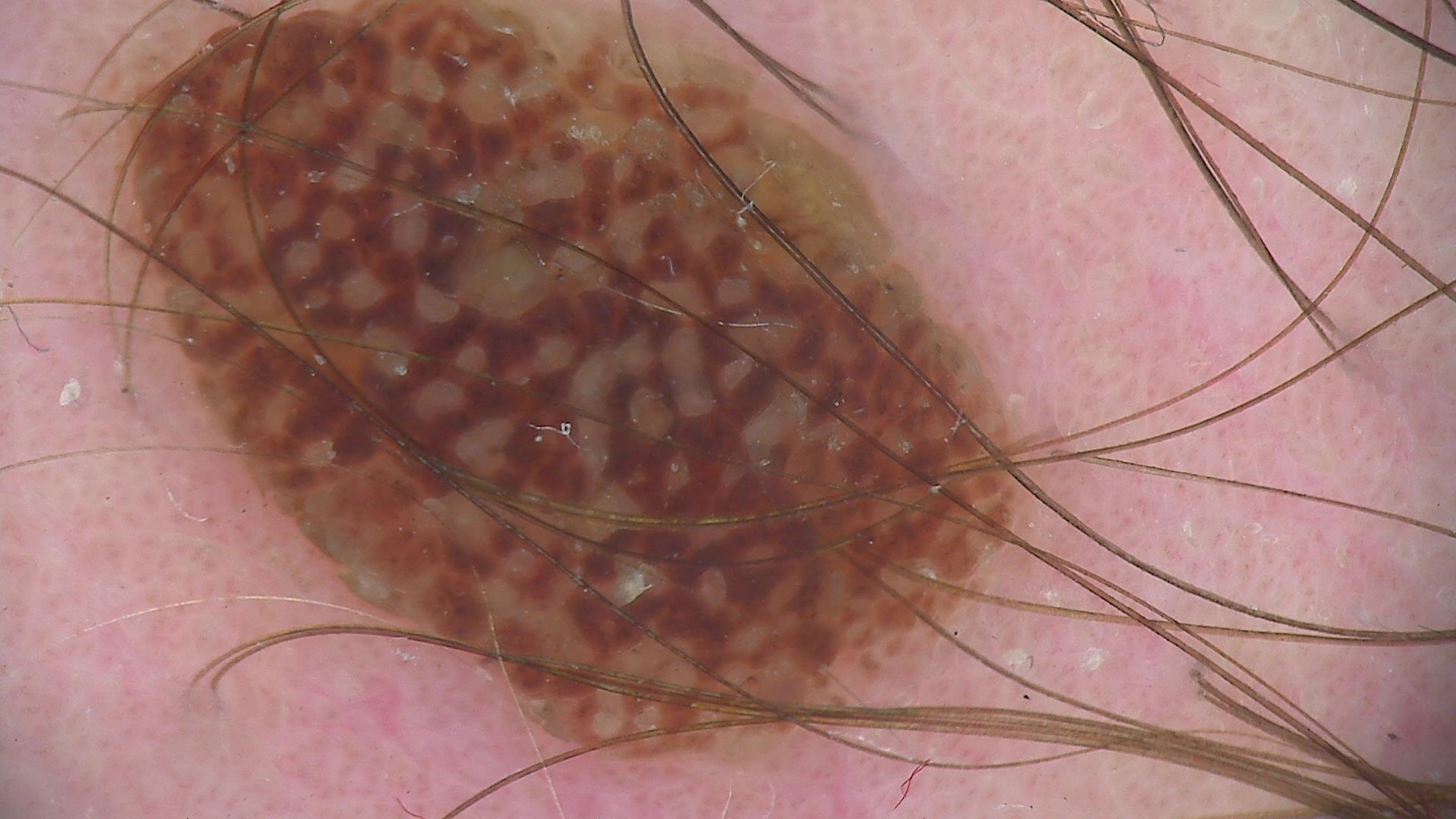Q: What kind of image is this?
A: dermatoscopy
Q: What kind of lesion is this?
A: banal
Q: What is the diagnosis?
A: compound nevus (expert consensus)